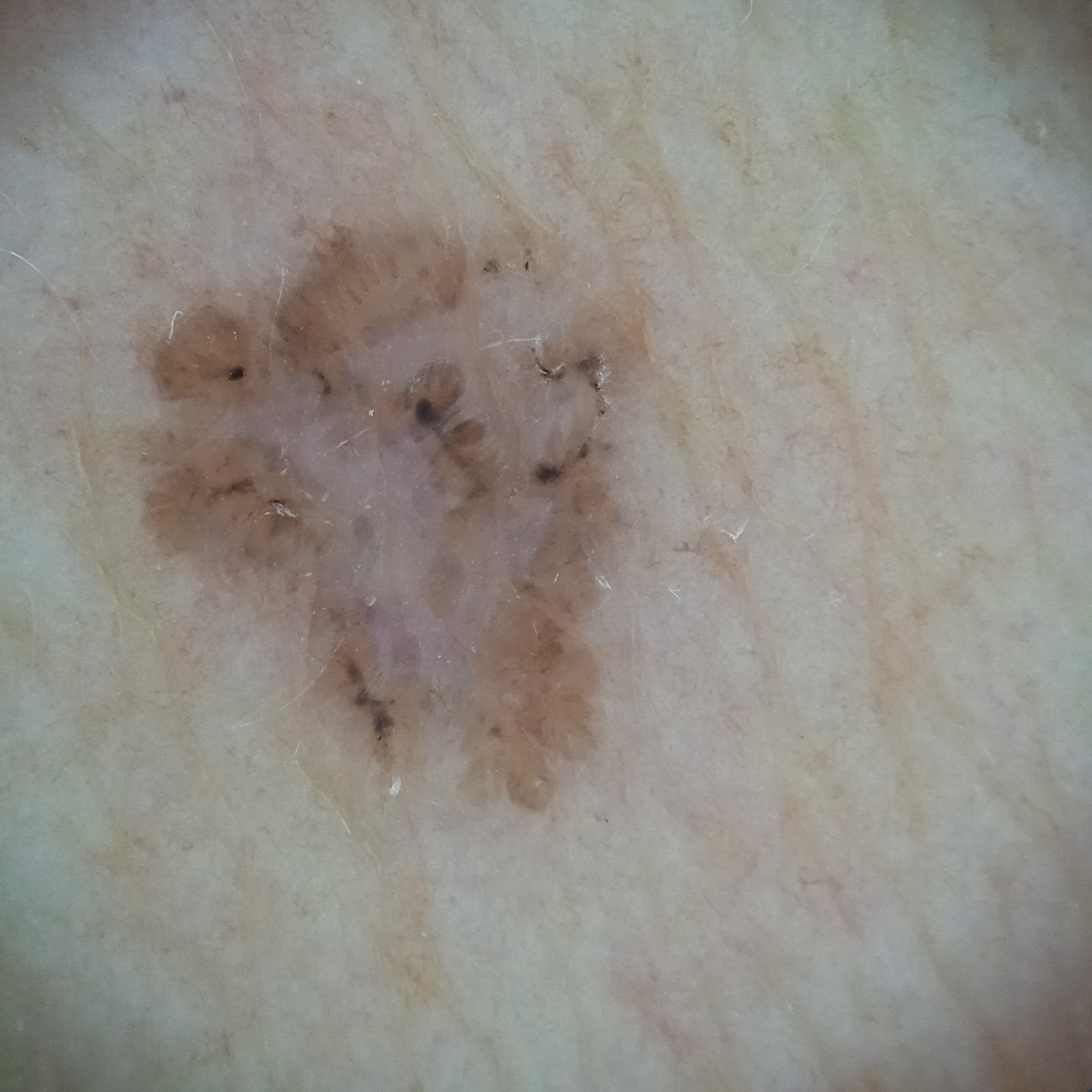On a questionnaire the patient reported a personal history of cancer and a personal history of skin cancer.
The patient describes having few moles overall.
The referring clinician suspected basal cell carcinoma.
The patient says their skin tans without first burning.
The lesion is located on the torso.
The dermatologists' assessment was a basal cell carcinoma.